A female subject, aged 18-22 · a dermoscopic close-up of a skin lesion.
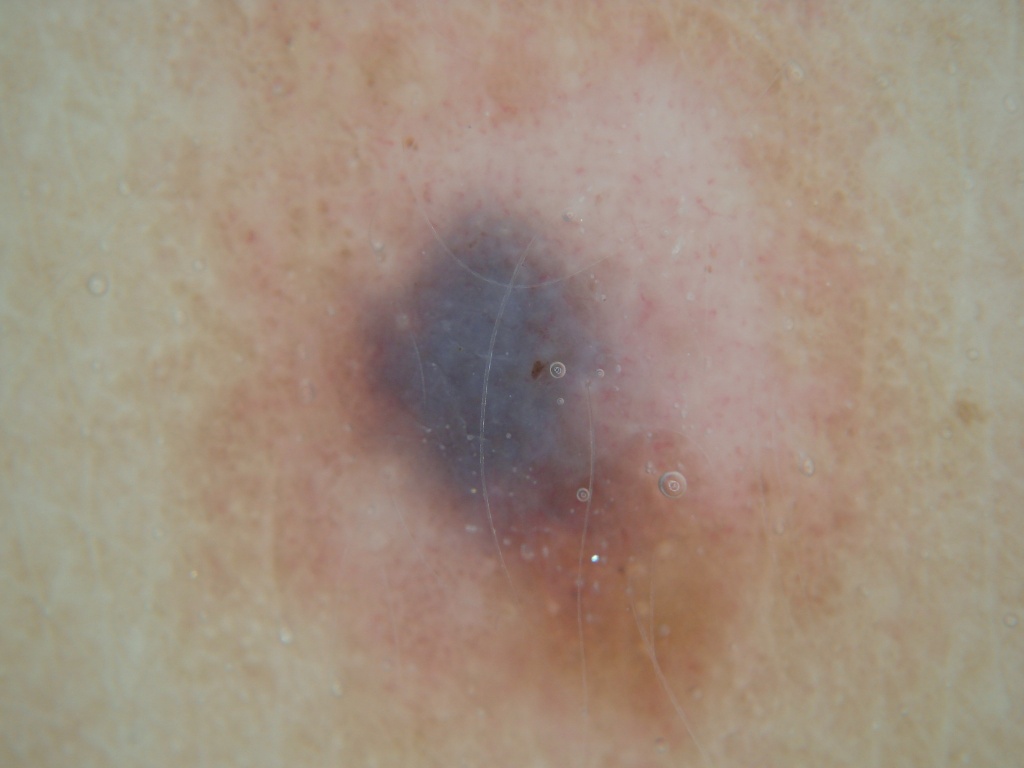The lesion takes up about 71% of the image. Dermoscopy demonstrates no globules, streaks, negative network, pigment network, or milia-like cysts. The lesion is bounded by x1=123 y1=1 x2=931 y2=766. Diagnosed as a melanocytic nevus, a benign lesion.